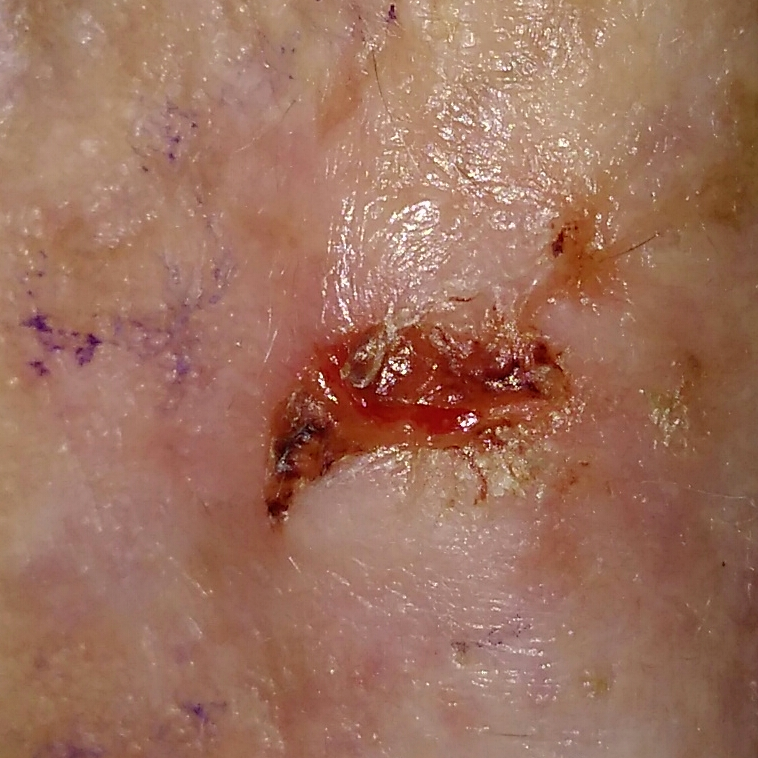Q: How was this image acquired?
A: clinical photograph
Q: Patient demographics?
A: female, 85 years of age
Q: Skin phototype?
A: III
Q: What are the lesion's dimensions?
A: 12 × 5 mm
Q: What does the patient describe?
A: pain, itching, growth, elevation, bleeding / no change in appearance
Q: What is this lesion?
A: basal cell carcinoma (biopsy-proven)